Located on the leg. The photograph is a close-up of the affected area — 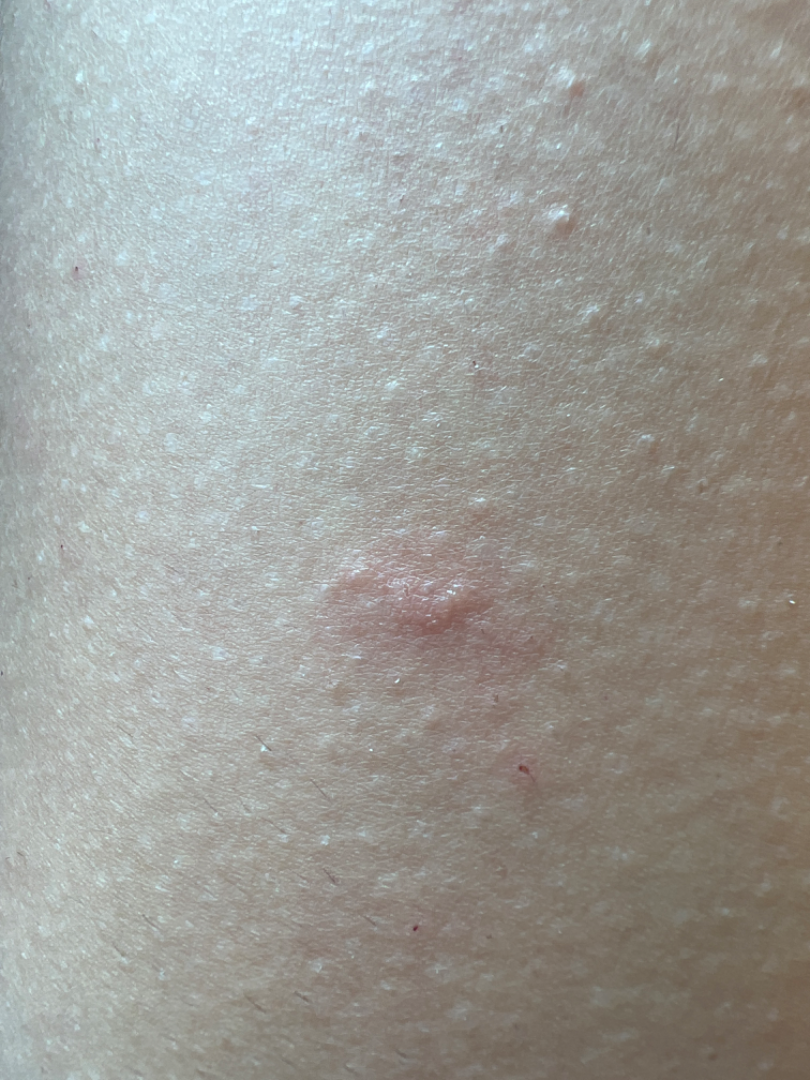History:
Reported lesion symptoms include itching. The patient described the issue as a rash. Fitzpatrick II. Present for less than one week. The patient reports the lesion is raised or bumpy.
Impression:
On teledermatology review: most likely Insect Bite.